Close-up view.
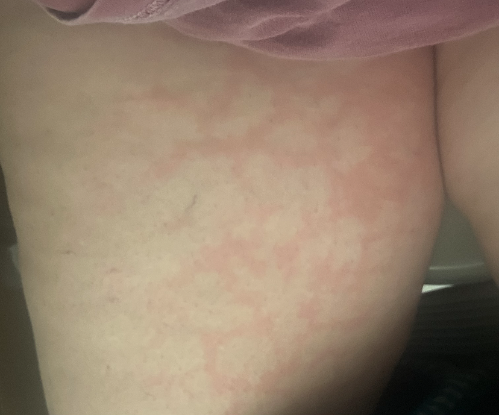diagnostic considerations = the primary impression is Livedo reticularis; an alternative is Erythema ab igne.